Acquired for a research image collection, with no referral diagnosis; the patient says their skin reddens painfully with sun exposure; few moles overall by the patient's own estimate; a female patient aged 48:
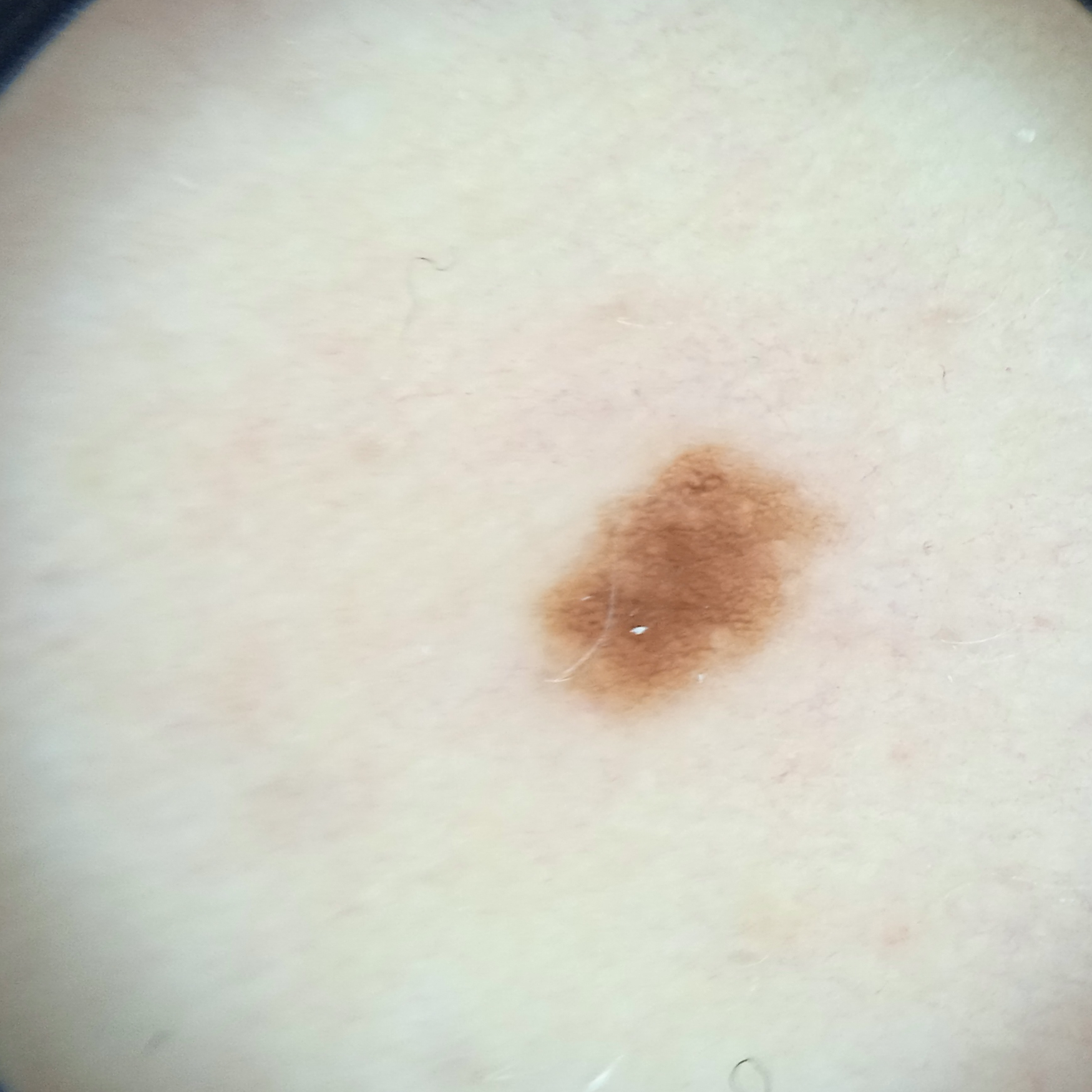anatomic site: the torso
lesion size: 4.3 mm
diagnosis: melanocytic nevus (dermatologist consensus)